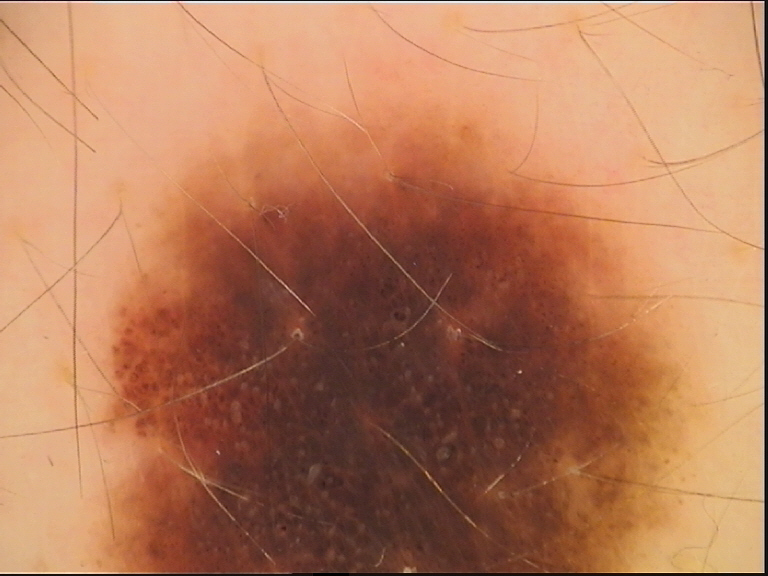| feature | finding |
|---|---|
| classification | banal |
| class | congenital compound nevus (expert consensus) |